A dermoscopy image of a single skin lesion.
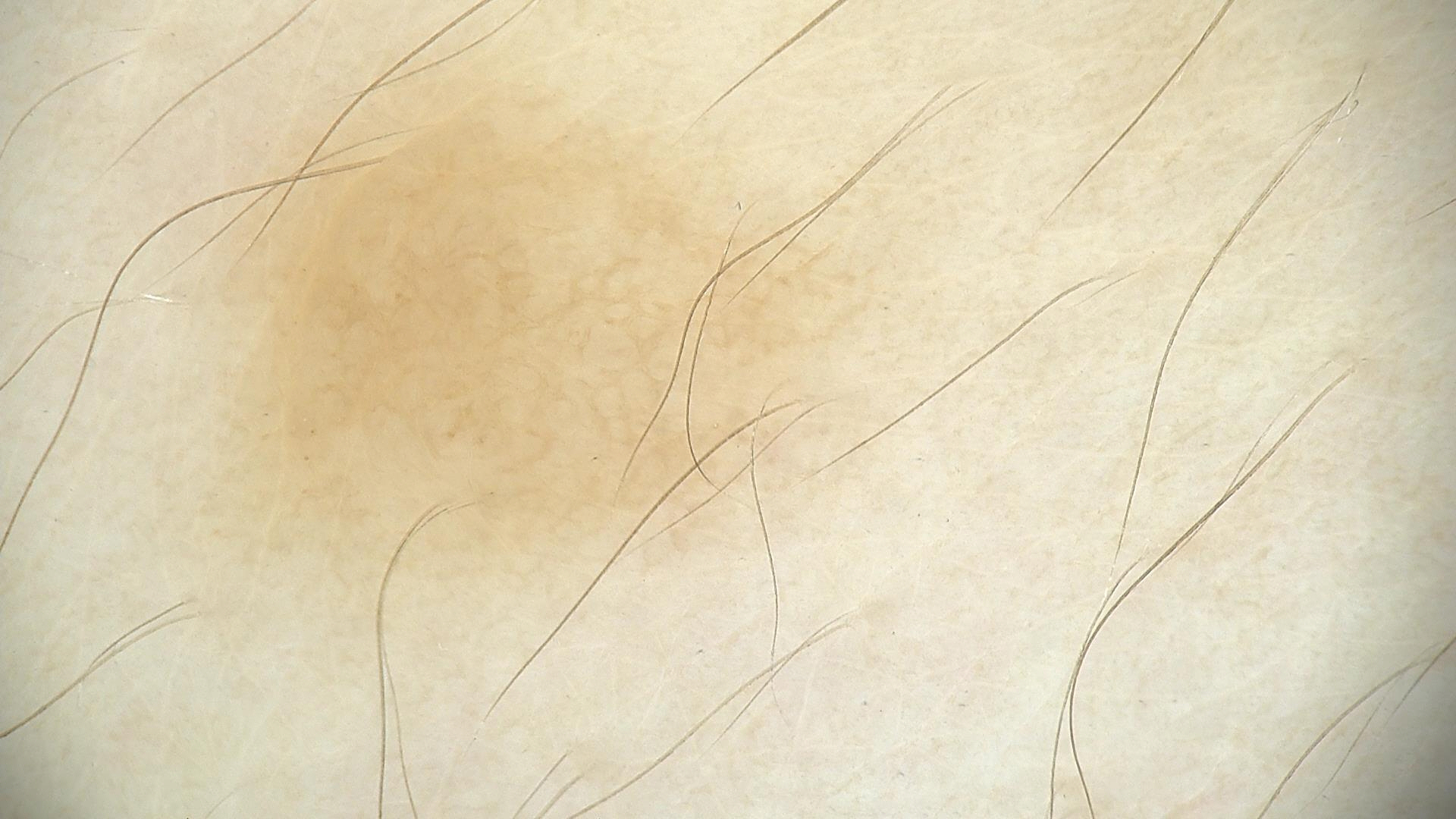{"diagnosis": {"name": "dermal nevus", "code": "db", "malignancy": "benign", "super_class": "melanocytic", "confirmation": "expert consensus"}}